A skin lesion imaged with a dermatoscope:
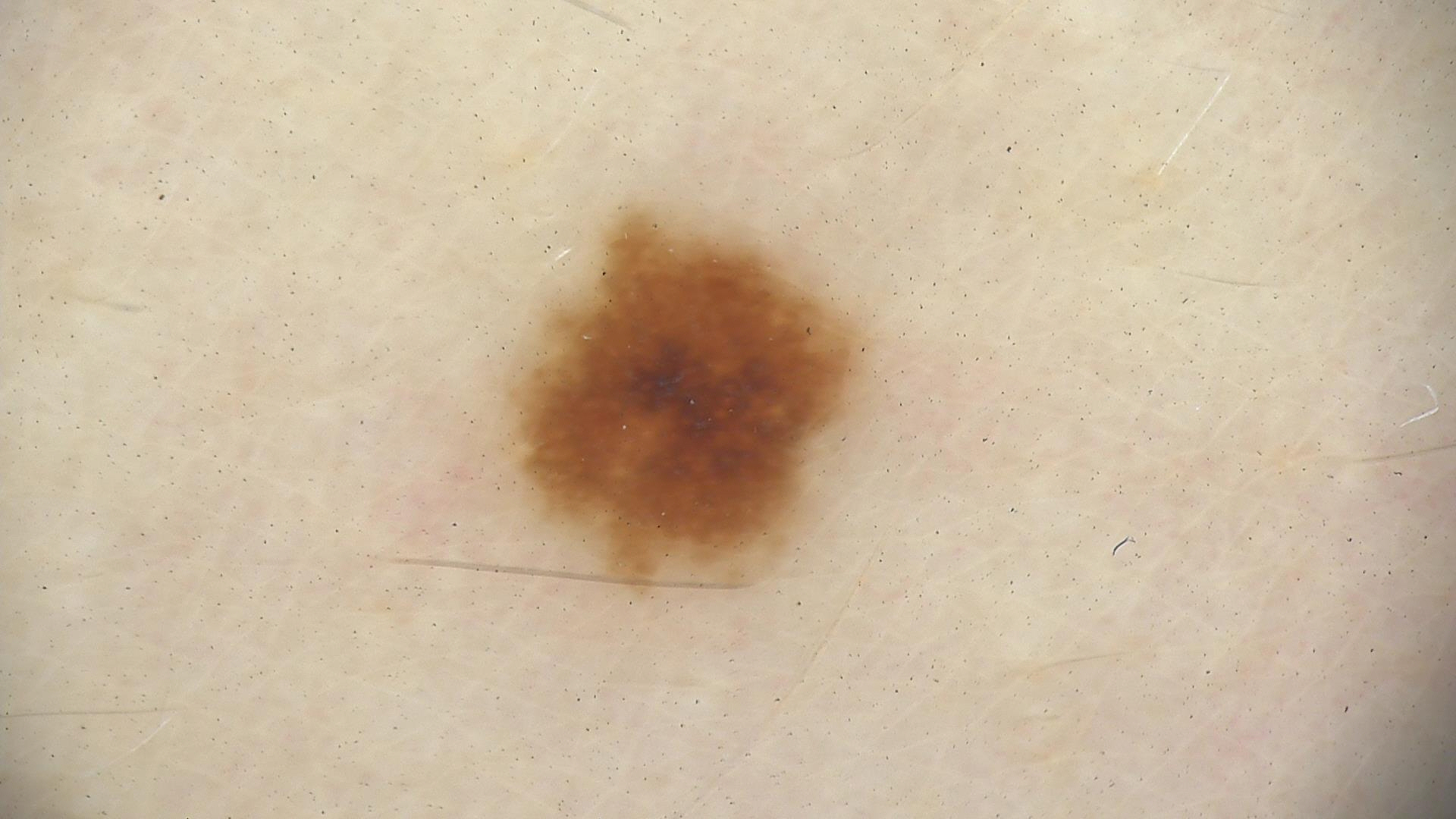assessment: dysplastic junctional nevus (expert consensus)